The front of the torso is involved · the photograph was taken at an angle.
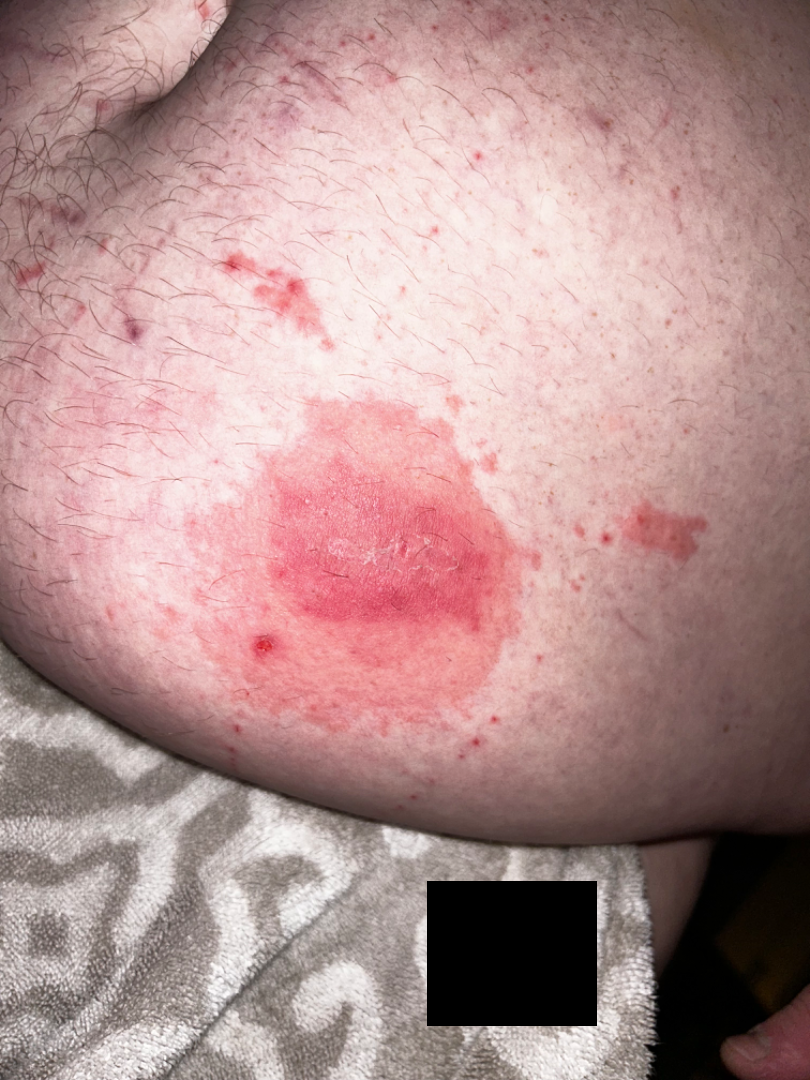{"assessment": "unable to determine", "texture": "rough or flaky", "systemic_symptoms": "none reported", "symptoms": ["itching", "enlargement"], "duration": "one to four weeks", "skin_tone": {"fitzpatrick": "III", "monk_skin_tone": 2}}